Fitzpatrick skin type II. A female patient aged 83 or older. A dermoscopic photograph of a skin lesion.
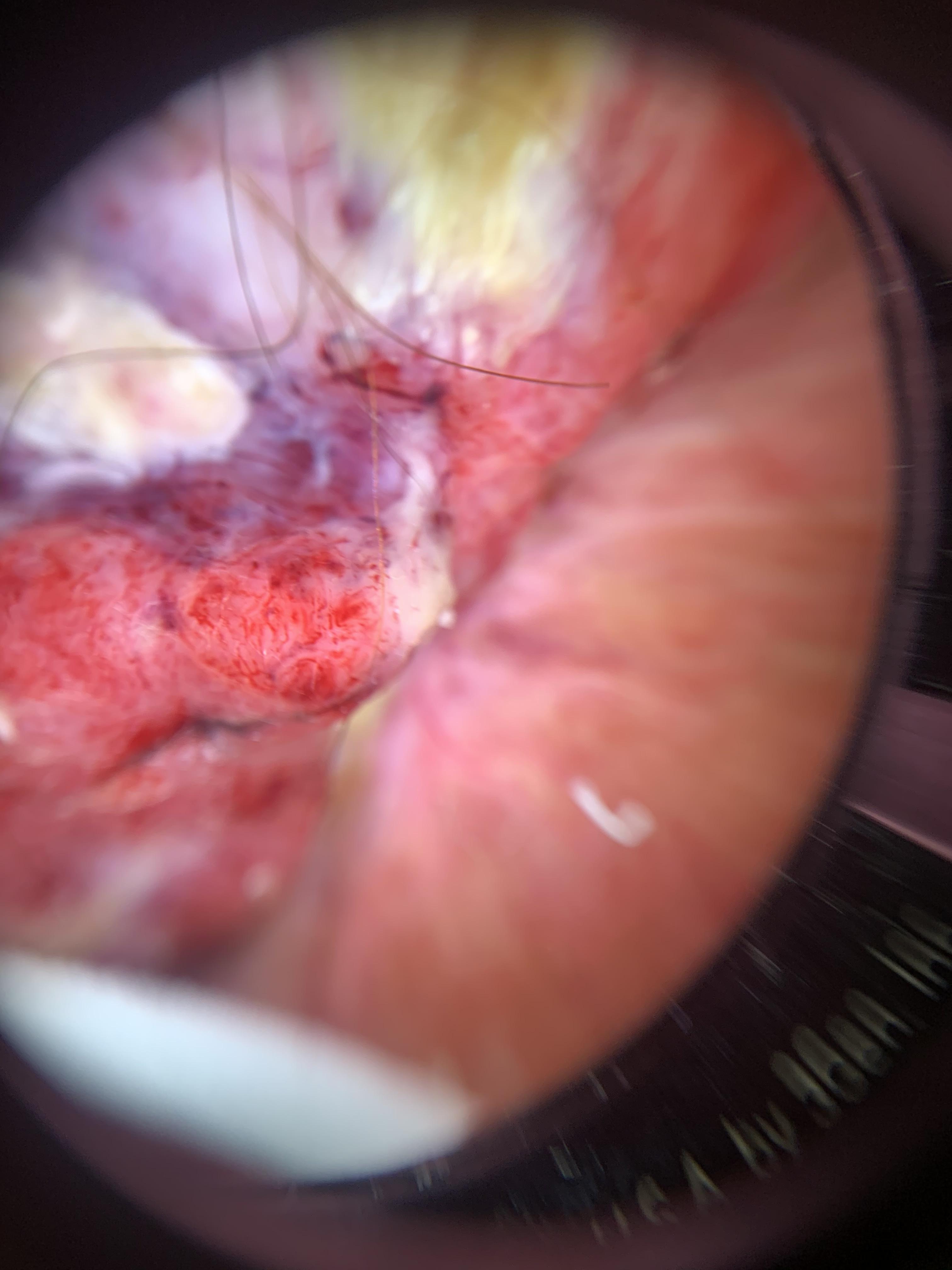Q: Where is the lesion located?
A: the head or neck
Q: What is the diagnosis?
A: Squamous cell carcinoma (biopsy-proven)